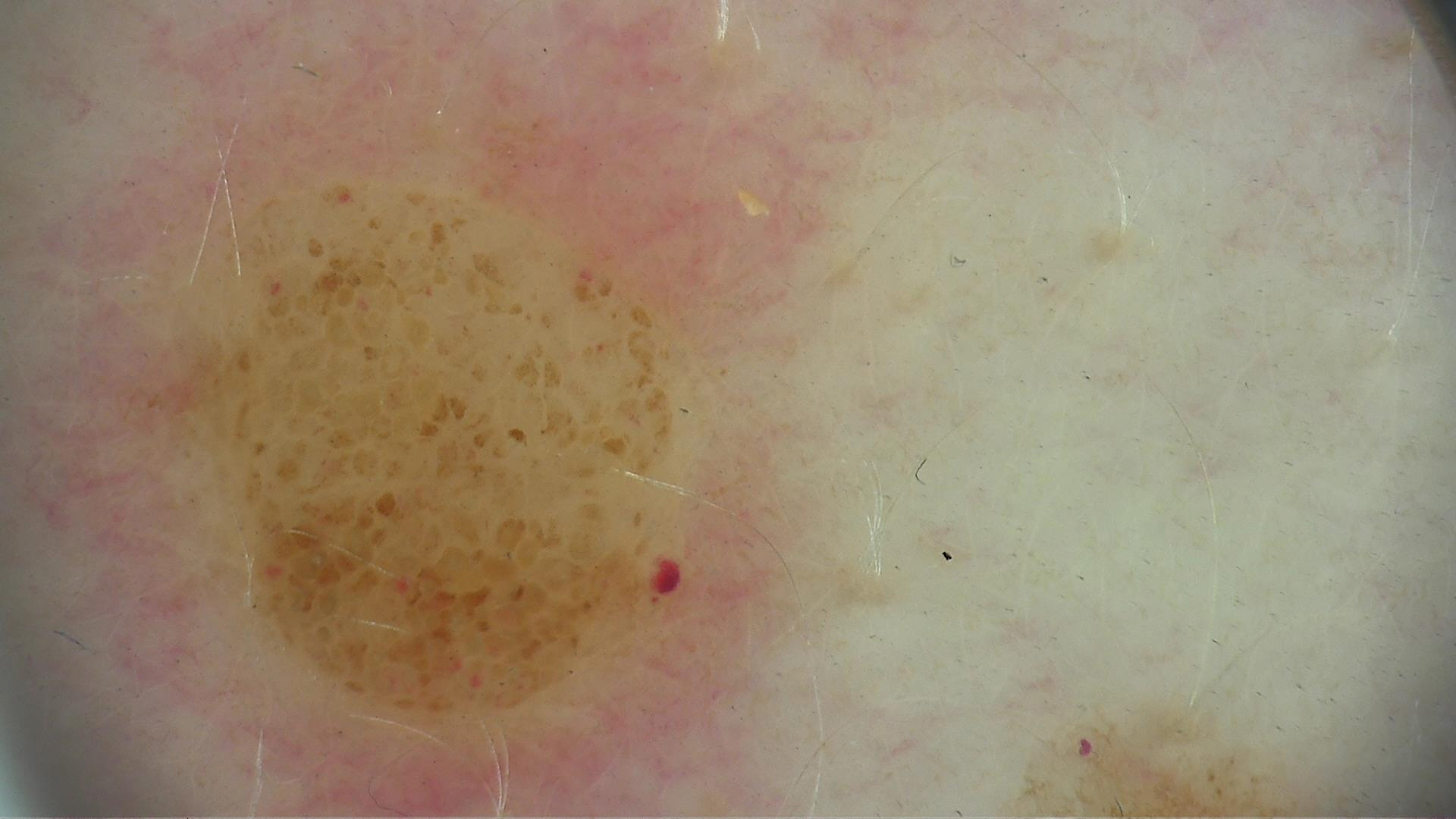Labeled as a banal lesion — a compound nevus.